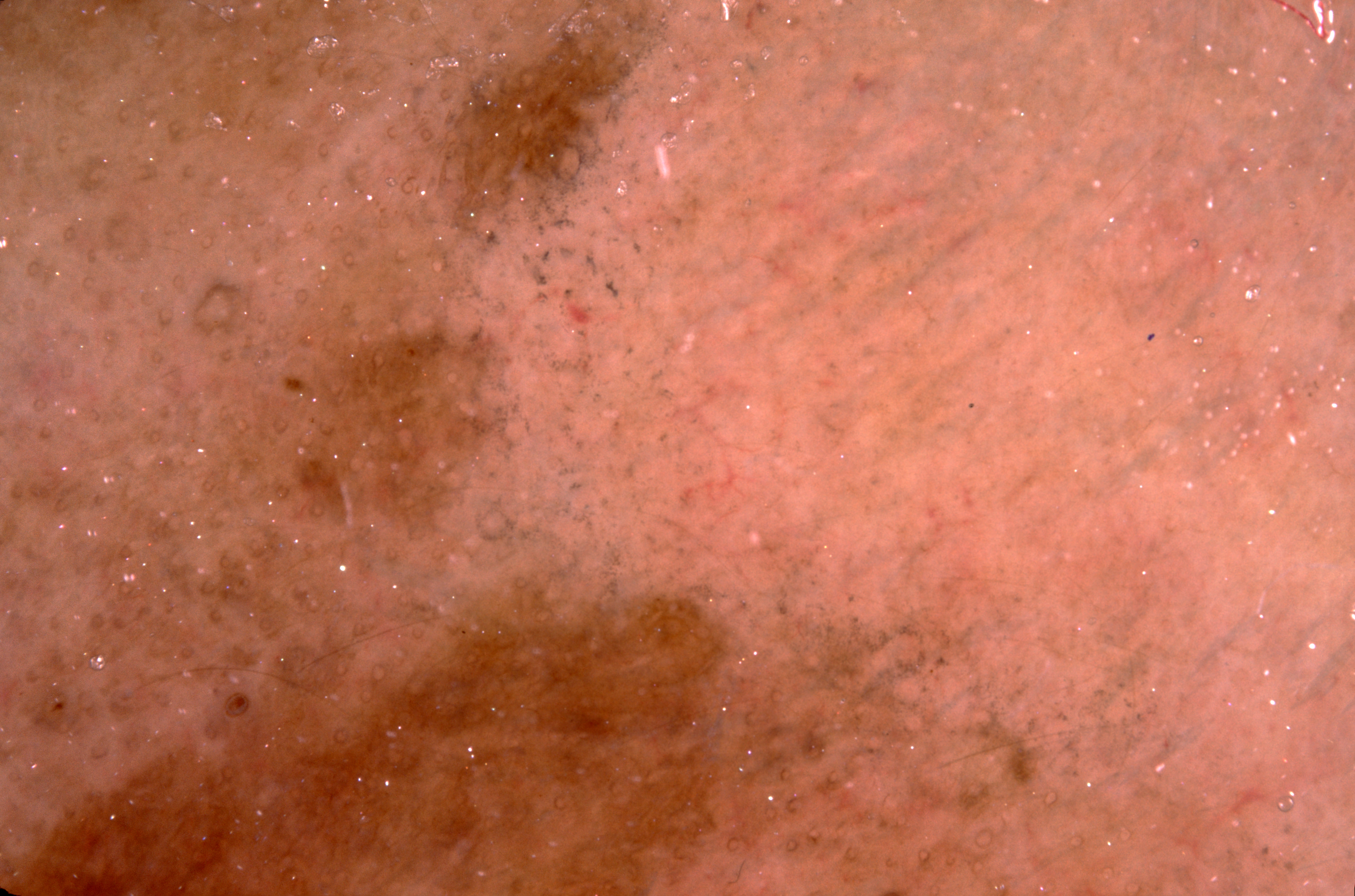| key | value |
|---|---|
| modality | dermoscopic image |
| patient | female, aged around 70 |
| lesion location | spans the dermoscopic field |
| absent dermoscopic features | milia-like cysts, negative network, streaks, and pigment network |
| impression | a melanocytic nevus |